The photograph is a close-up of the affected area; the contributor is 18–29, male — 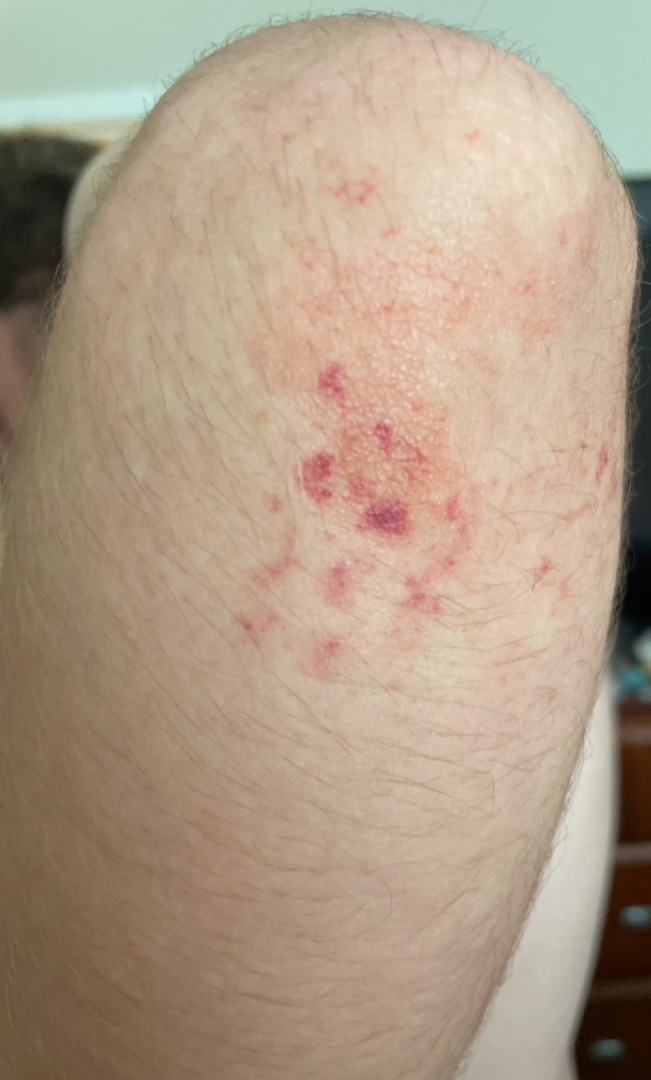{"differential": {"tied_lead": ["Contact dermatitis", "Purpura"], "unlikely": ["Pigmented purpuric eruption", "ecchymoses"]}}